A skin lesion imaged with a dermatoscope: 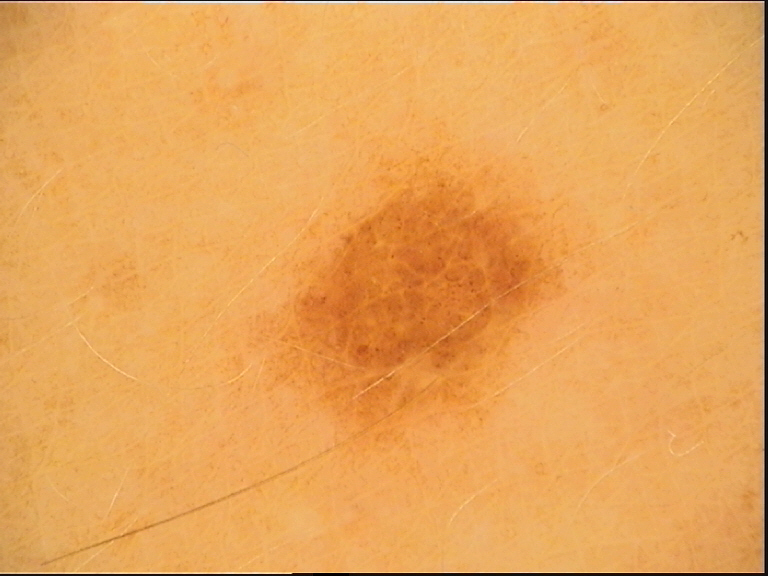Findings: The morphology is that of a banal lesion. Conclusion: The diagnosis was a compound nevus.